A dermatoscopic image of a skin lesion.
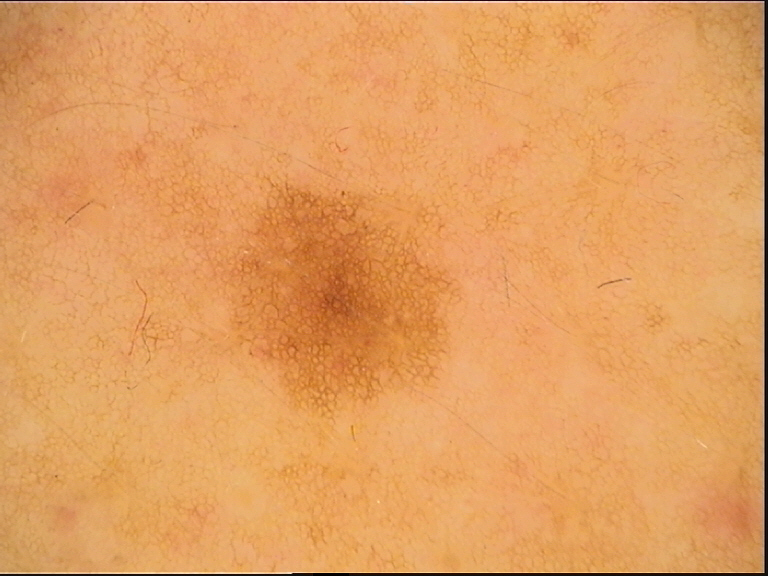subtype = banal, class = junctional nevus (expert consensus).